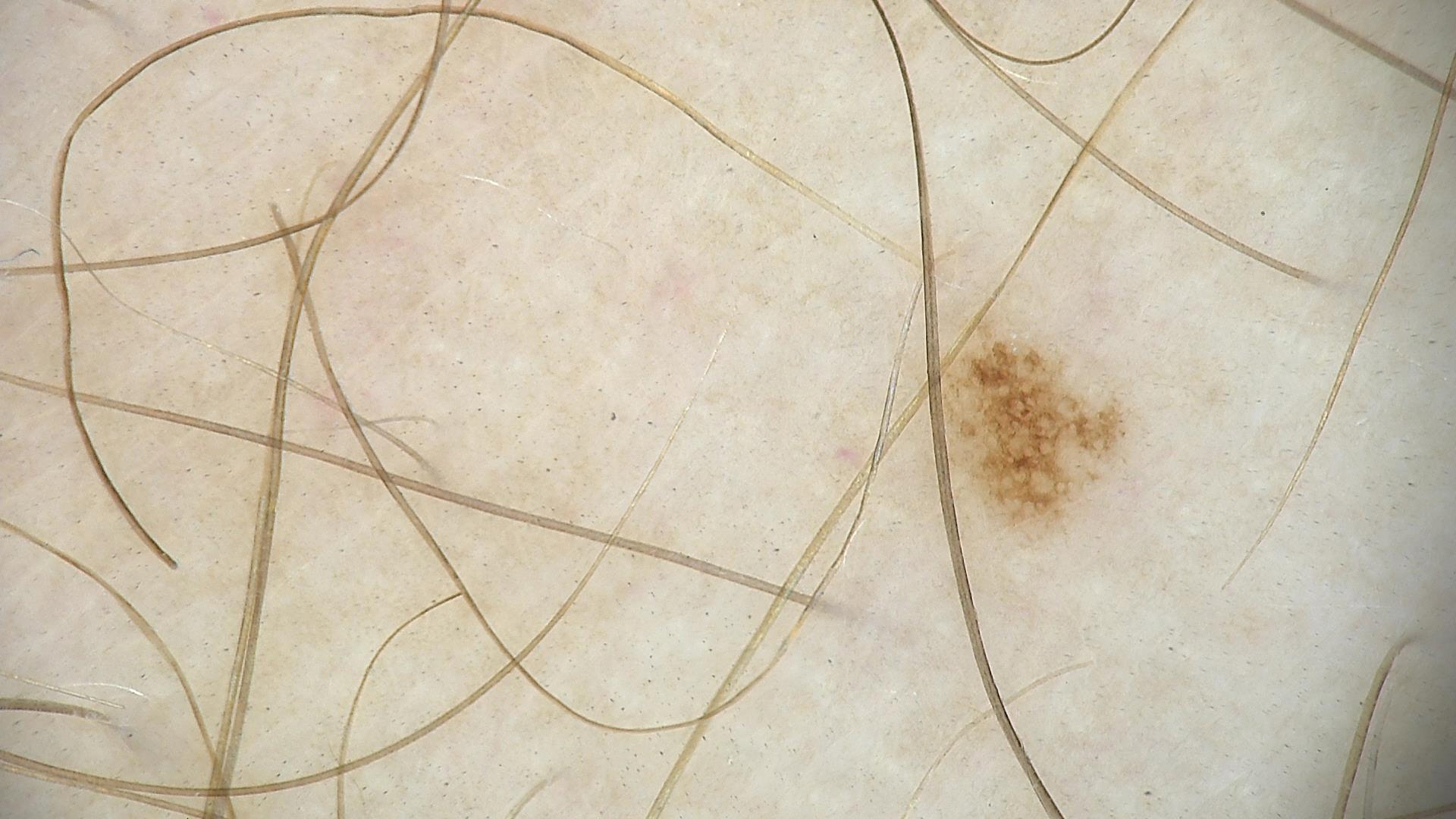diagnosis:
  name: dysplastic junctional nevus
  code: jd
  malignancy: benign
  super_class: melanocytic
  confirmation: expert consensus